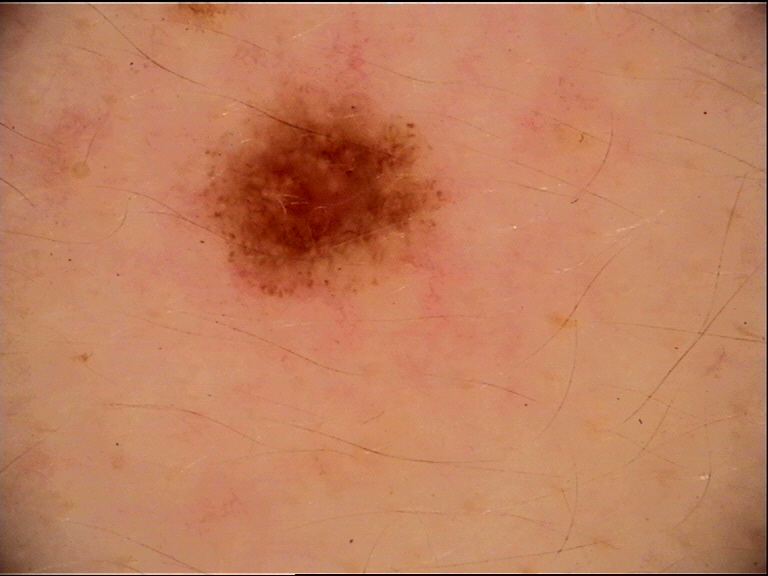Labeled as a dysplastic junctional nevus.